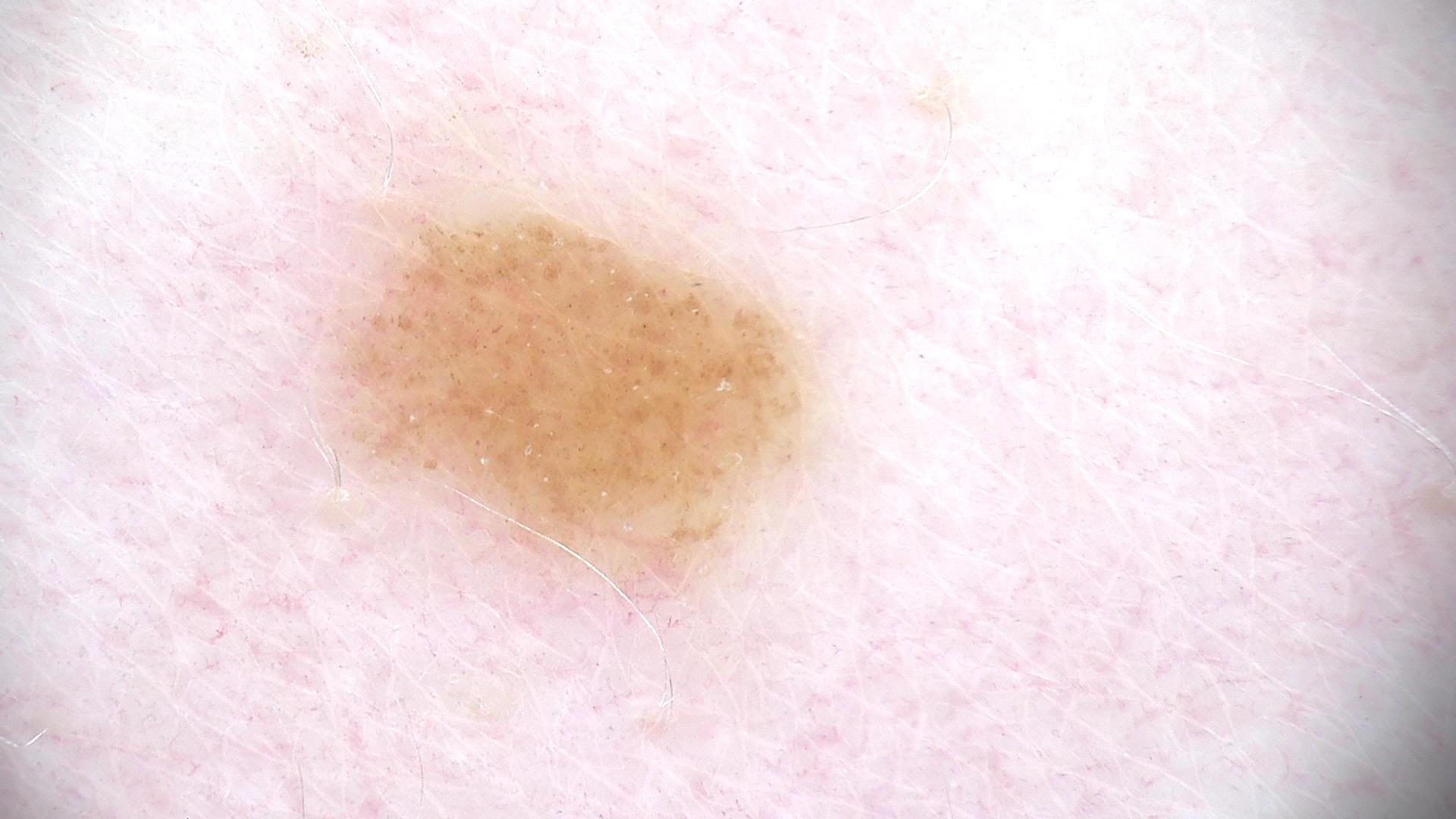Consistent with a junctional nevus.